This image was taken at a distance. Located on the head or neck, front of the torso and back of the torso. Male contributor, age 18–29: 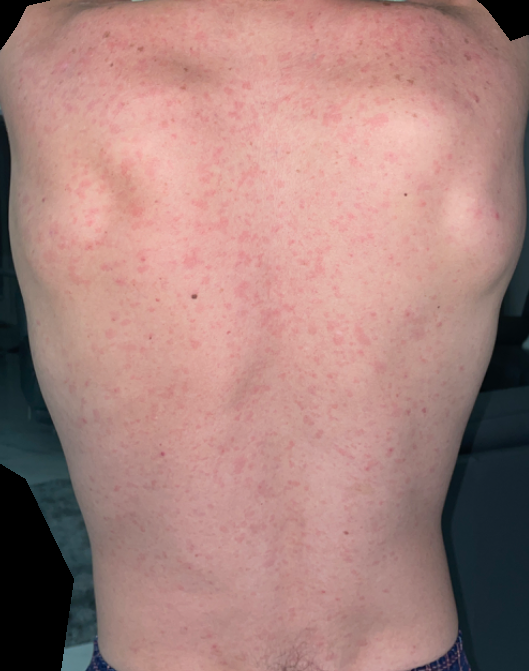Drug Rash (0.67); Viral Exanthem (0.33).